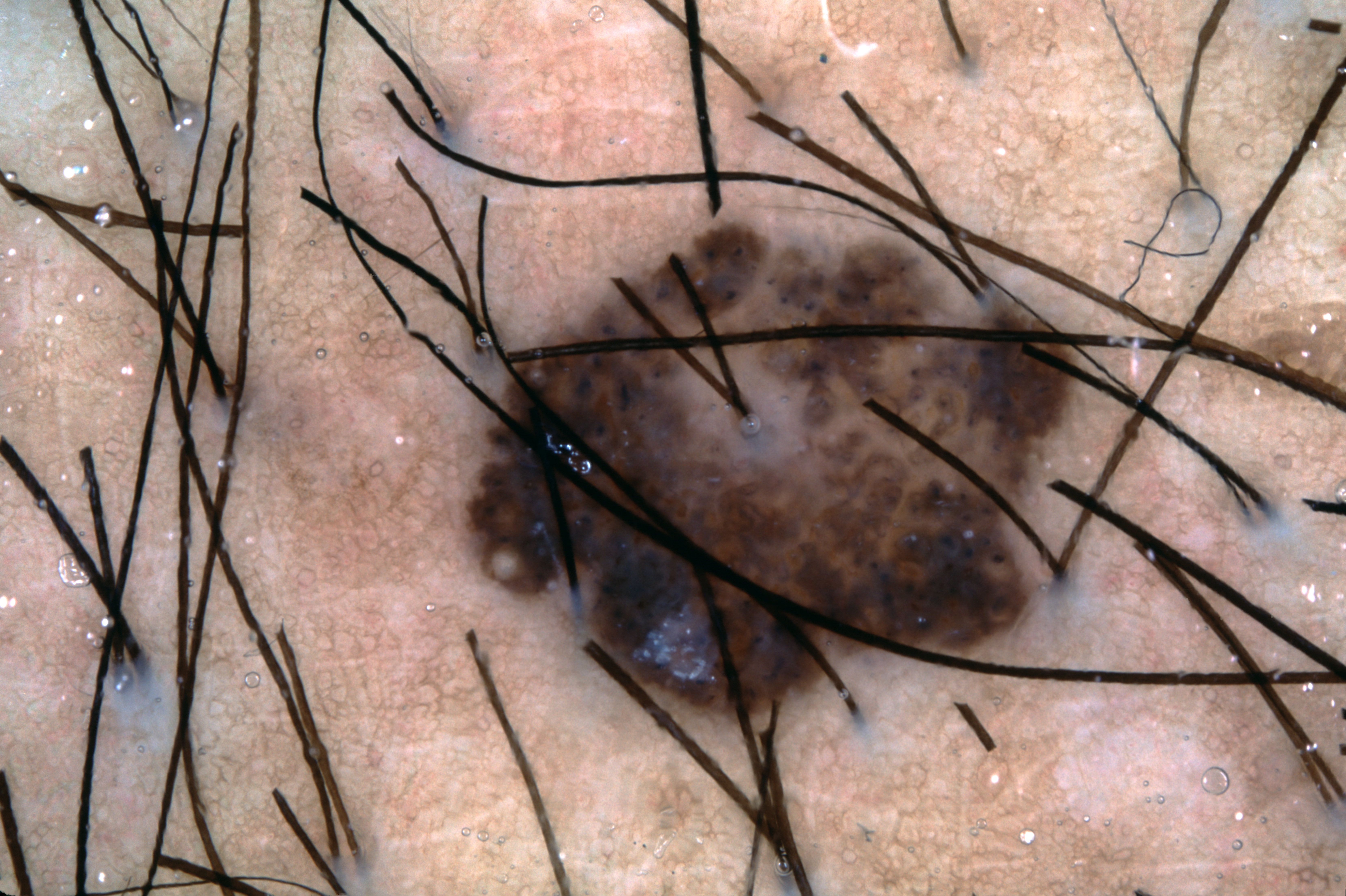This is a dermoscopic photograph of a skin lesion. Dermoscopic examination shows milia-like cysts. A moderately sized lesion. As (left, top, right, bottom), the visible lesion spans (463, 217, 1104, 735). Clinically diagnosed as a seborrheic keratosis, a benign lesion.